A clinical close-up of a skin lesion — 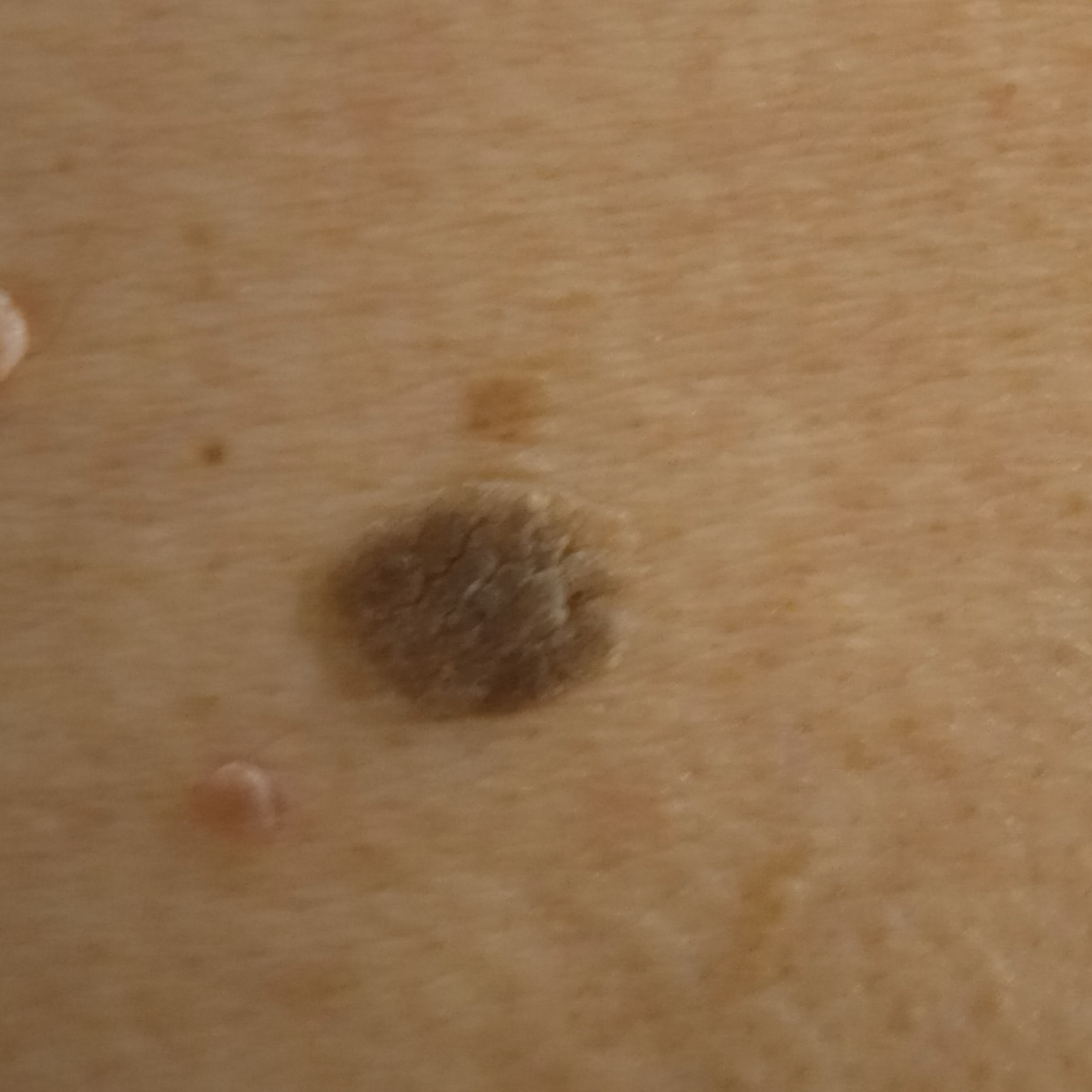anatomic site: the back
diameter: 10.2 mm
diagnostic label: seborrheic keratosis (dermatologist consensus)